A male subject approximately 40 years of age; a skin lesion imaged with contact-polarized dermoscopy:
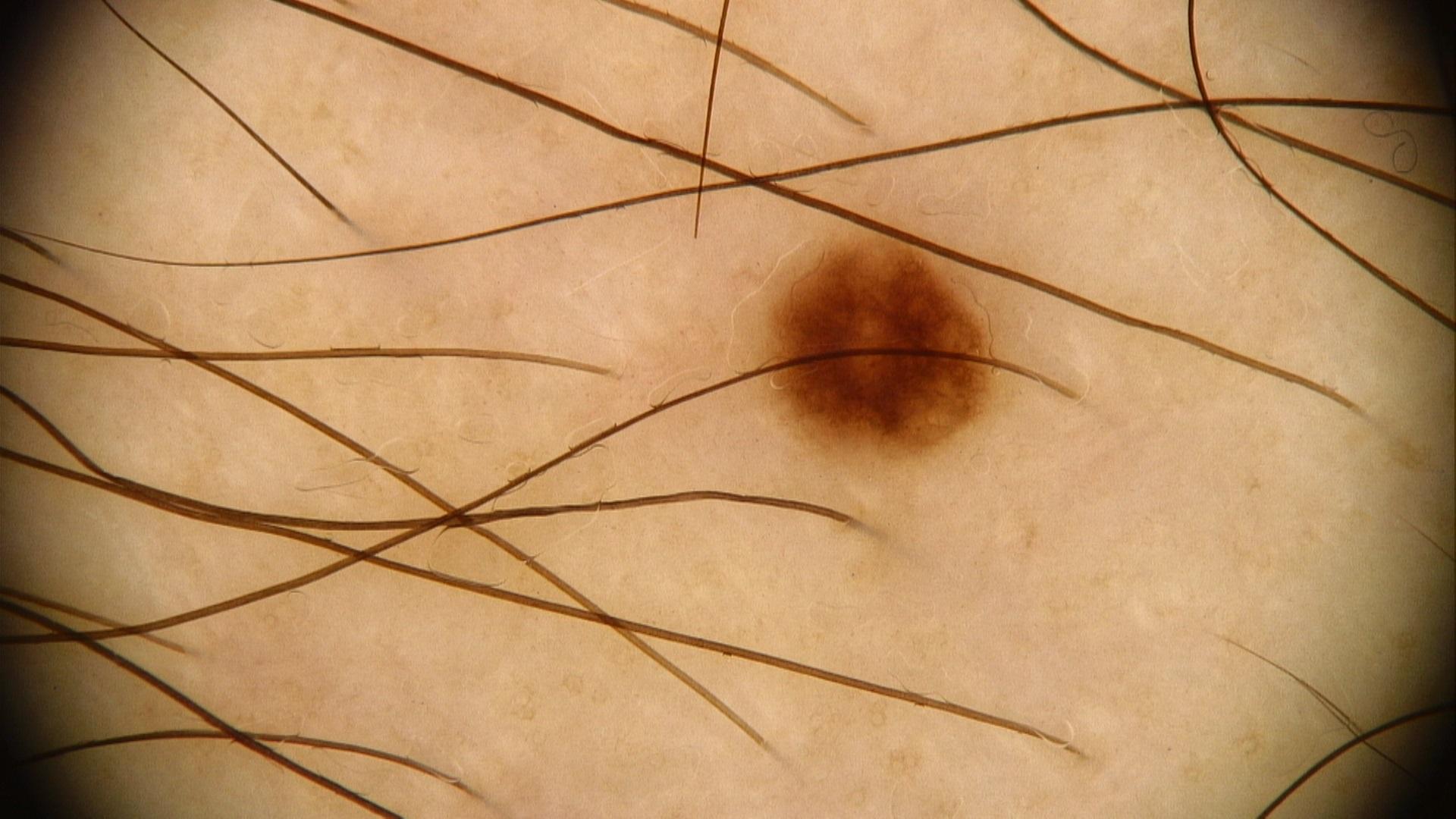Case summary: The lesion was found on the trunk. Impression: Clinically diagnosed as a nevus.